A dermoscopy image of a single skin lesion: 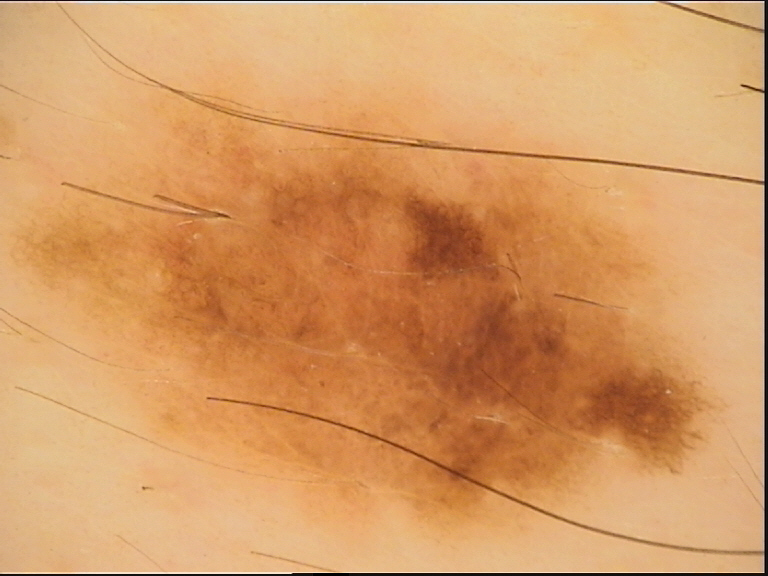Conclusion: The diagnostic label was a benign lesion — a dysplastic junctional nevus.